A dermoscopic photograph of a skin lesion: 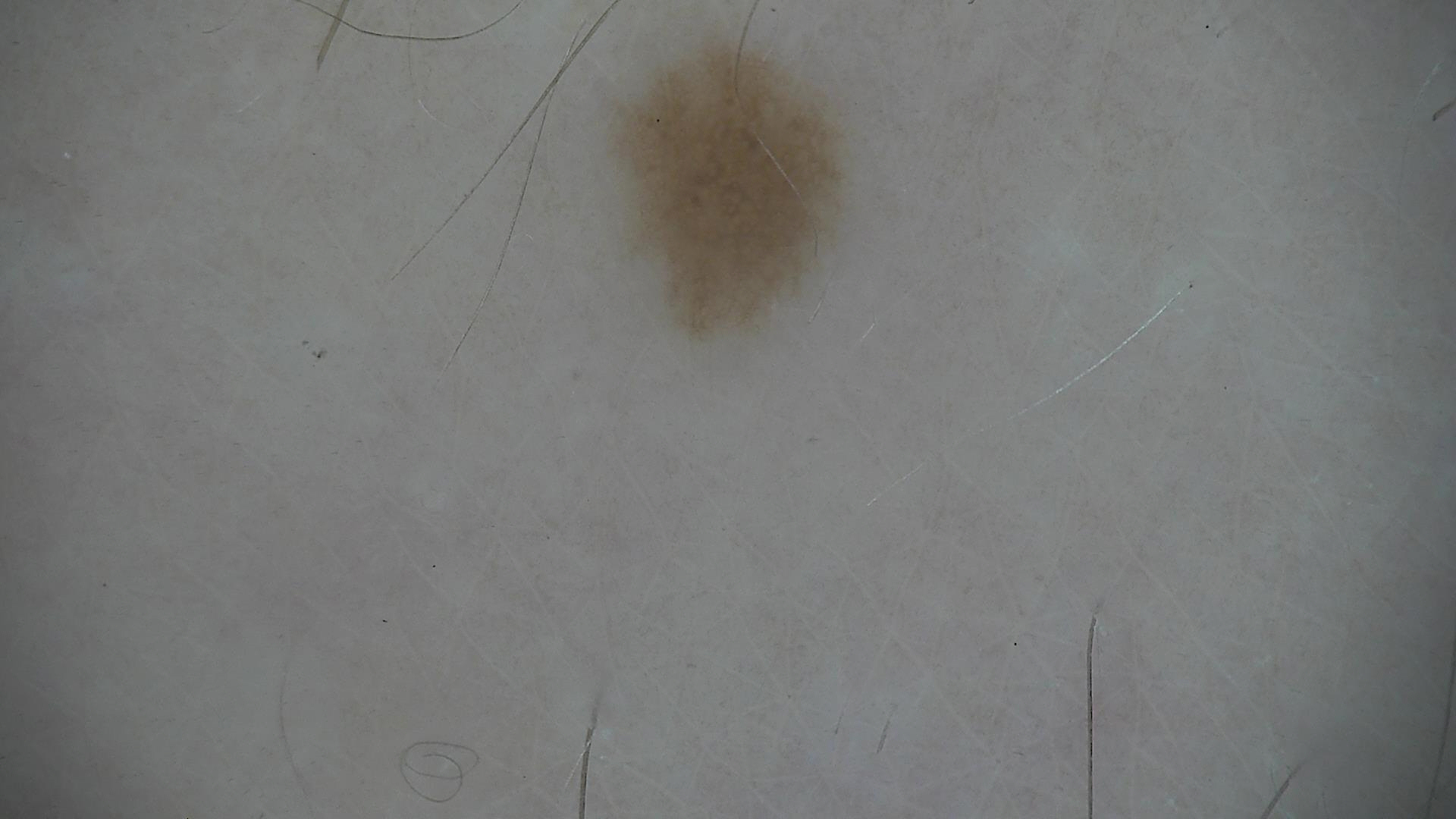Case:
• diagnostic label: dysplastic junctional nevus (expert consensus)